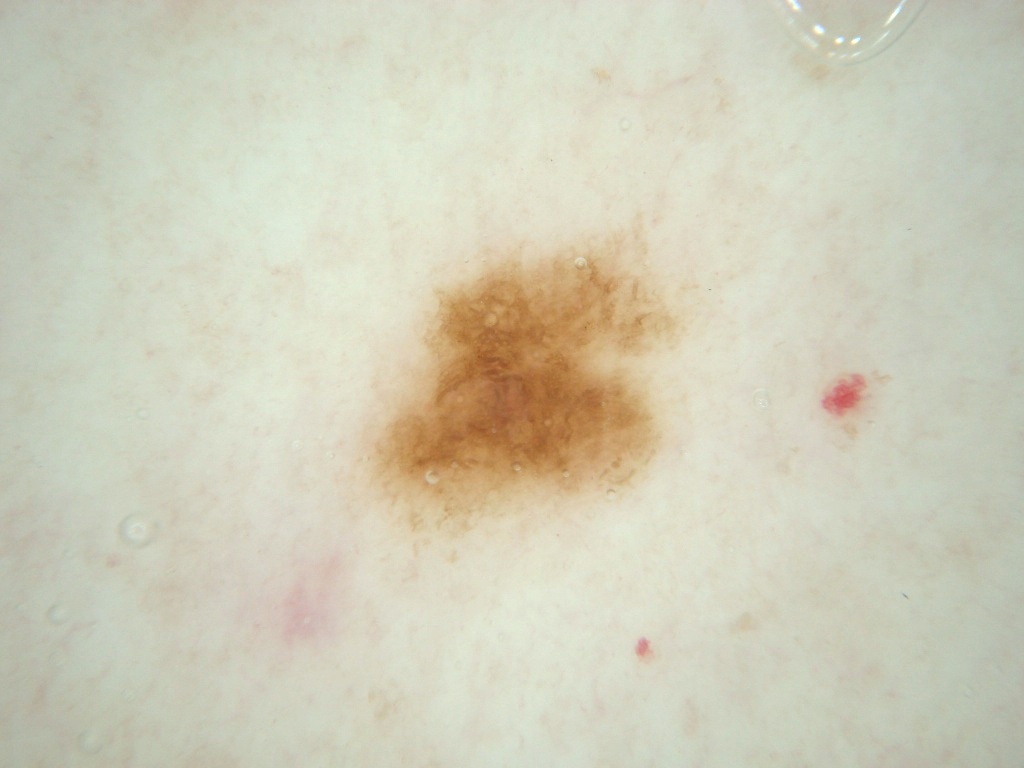Case summary: A skin lesion imaged with a dermatoscope. In (x1, y1, x2, y2) order, the lesion is located at <bbox>343, 220, 698, 549</bbox>. Dermoscopic assessment notes no globules or streaks. A mid-sized lesion within the field. Conclusion: Clinically diagnosed as a benign lesion.